A dermoscopic photograph of a skin lesion.
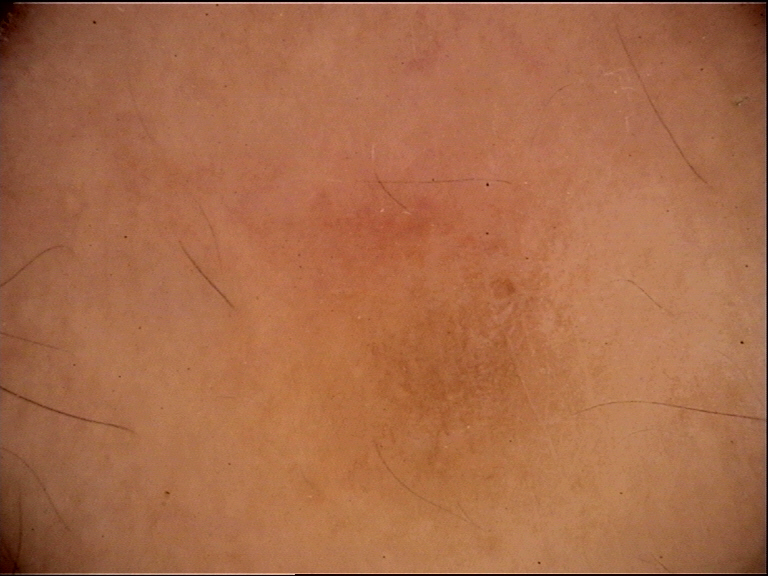class: dermatofibroma (expert consensus).